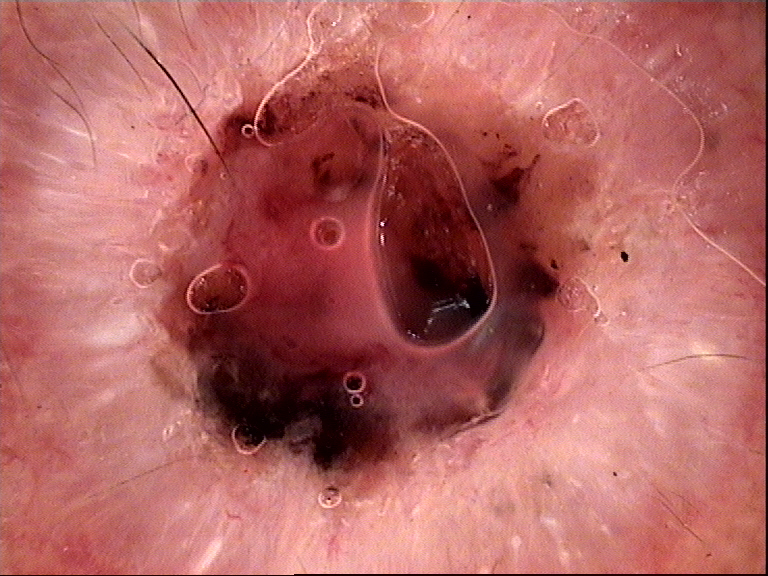modality: dermoscopy | subtype: keratinocytic | class: basal cell carcinoma (biopsy-proven).